By self-report, a personal history of cancer and a family history of skin cancer · the patient says their skin tans without first burning · a macroscopic clinical photograph of a skin lesion · a female subject aged 92 · collected as part of a research study, without a referral diagnosis — 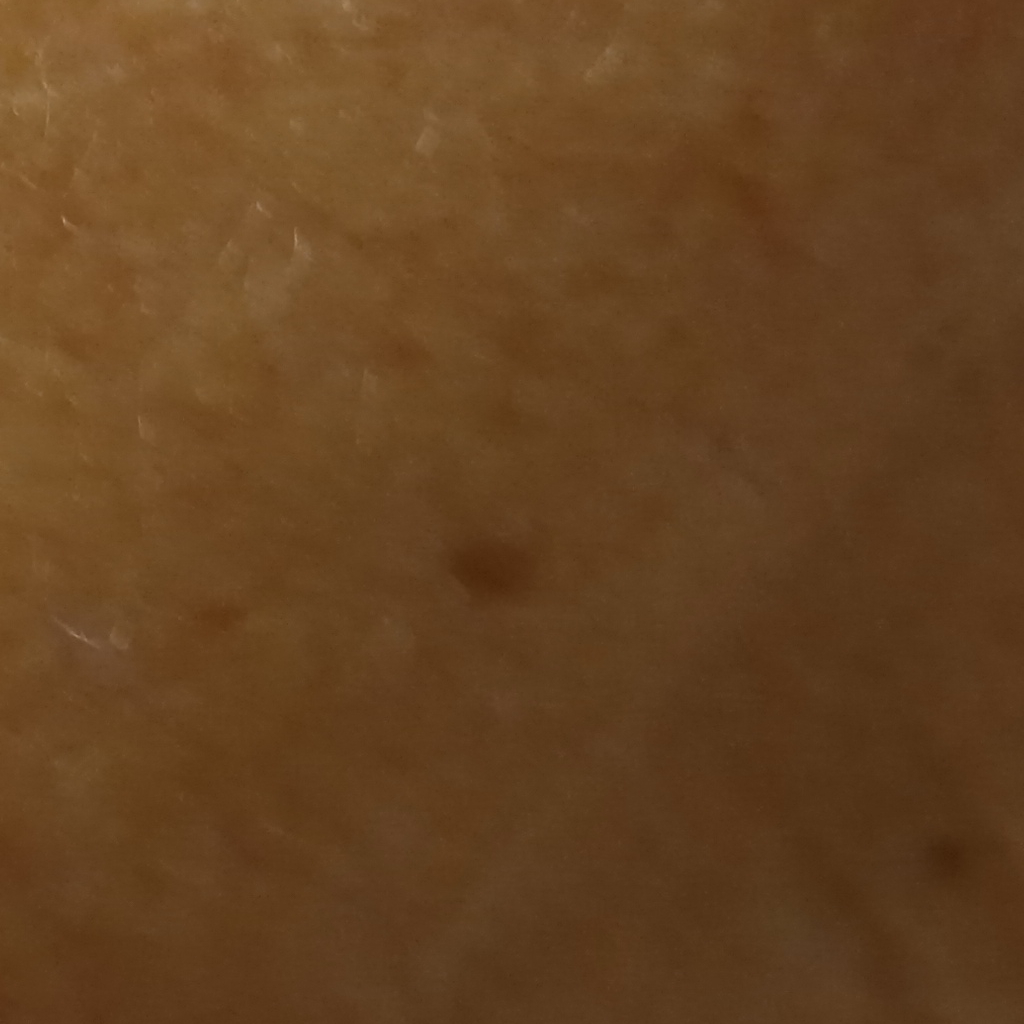The lesion is located on the face. The lesion measures approximately 2.9 mm. The dermatologists' assessment was a melanocytic nevus.